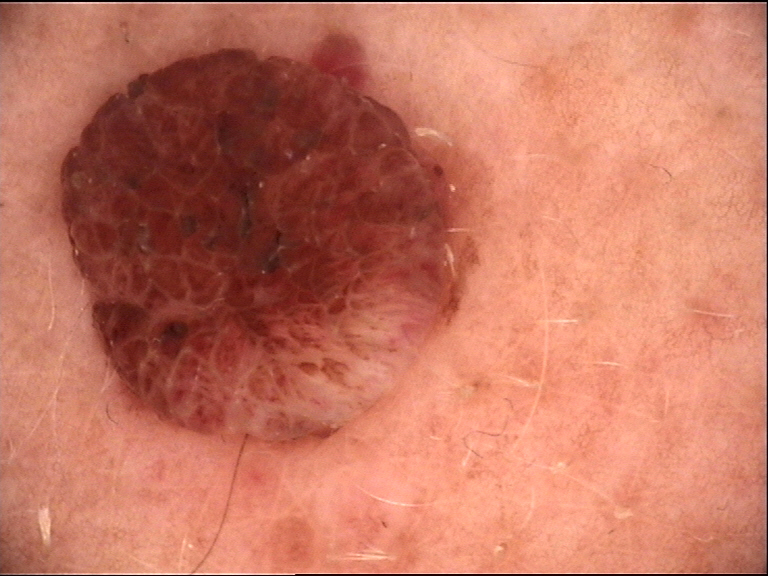<dermoscopy>
<diagnosis>
<name>dermal nevus</name>
<code>db</code>
<malignancy>benign</malignancy>
<super_class>melanocytic</super_class>
<confirmation>expert consensus</confirmation>
</diagnosis>
</dermoscopy>